A close-up photograph · the top or side of the foot and sole of the foot are involved · the subject is 18–29, male: 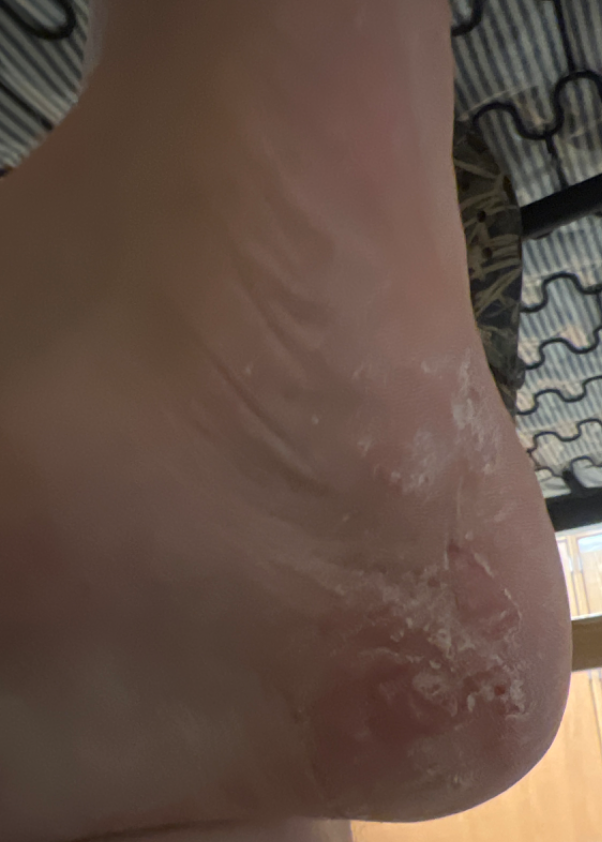Case summary:
- assessment: indeterminate from the photograph
- texture: fluid-filled and rough or flaky
- onset: three to twelve months
- patient's own categorization: a rash
- patient-reported symptoms: pain, bleeding, burning and itching
- systemic symptoms: joint pain, fatigue and shortness of breath
- skin tone: Fitzpatrick II